The subject is male. Located on the head or neck. The photo was captured at a distance.
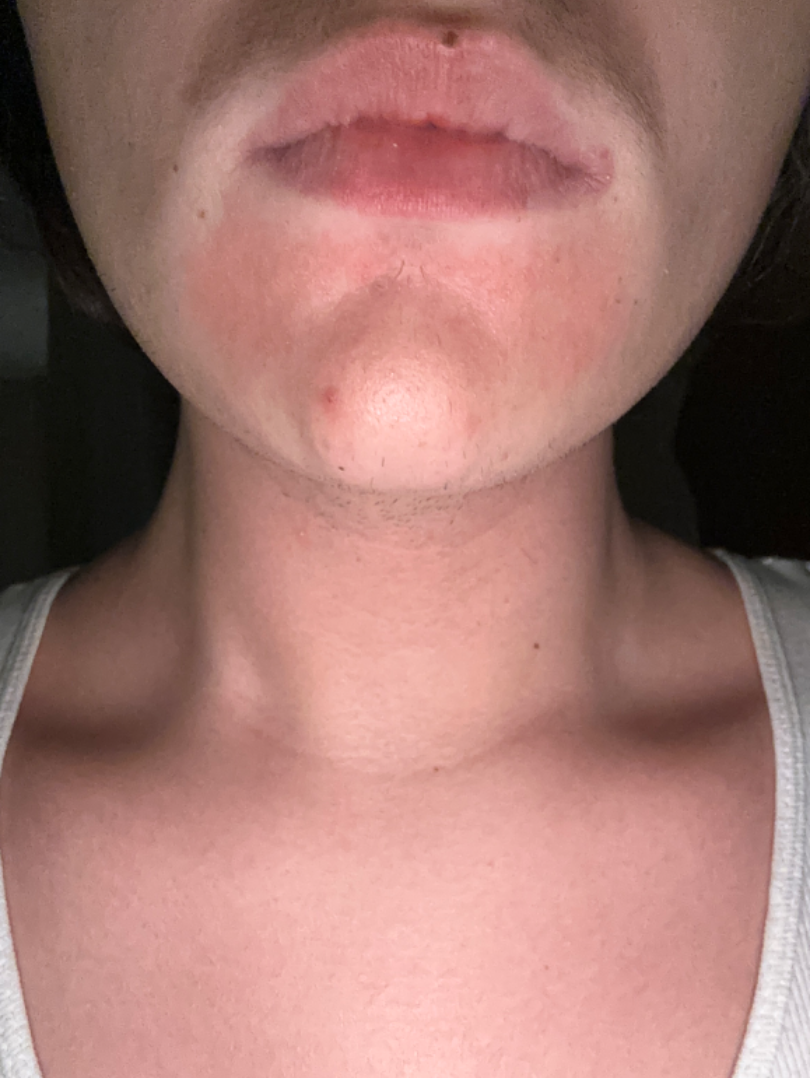<summary>
<symptoms>bothersome appearance</symptoms>
<patient_category>acne</patient_category>
<differential>
  <tied_lead>Perioral Dermatitis, Allergic Contact Dermatitis, Irritant Contact Dermatitis</tied_lead>
</differential>
</summary>